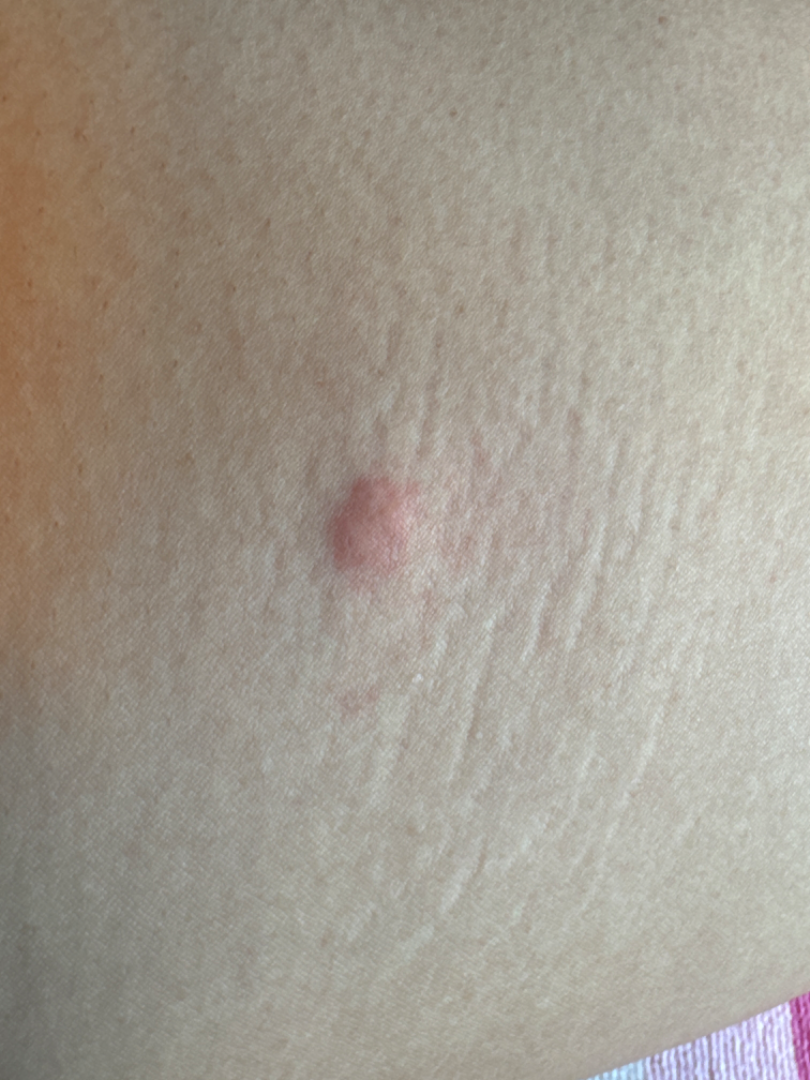The reviewer was unable to grade this case for skin condition. A close-up photograph. The leg is involved. The patient is female.